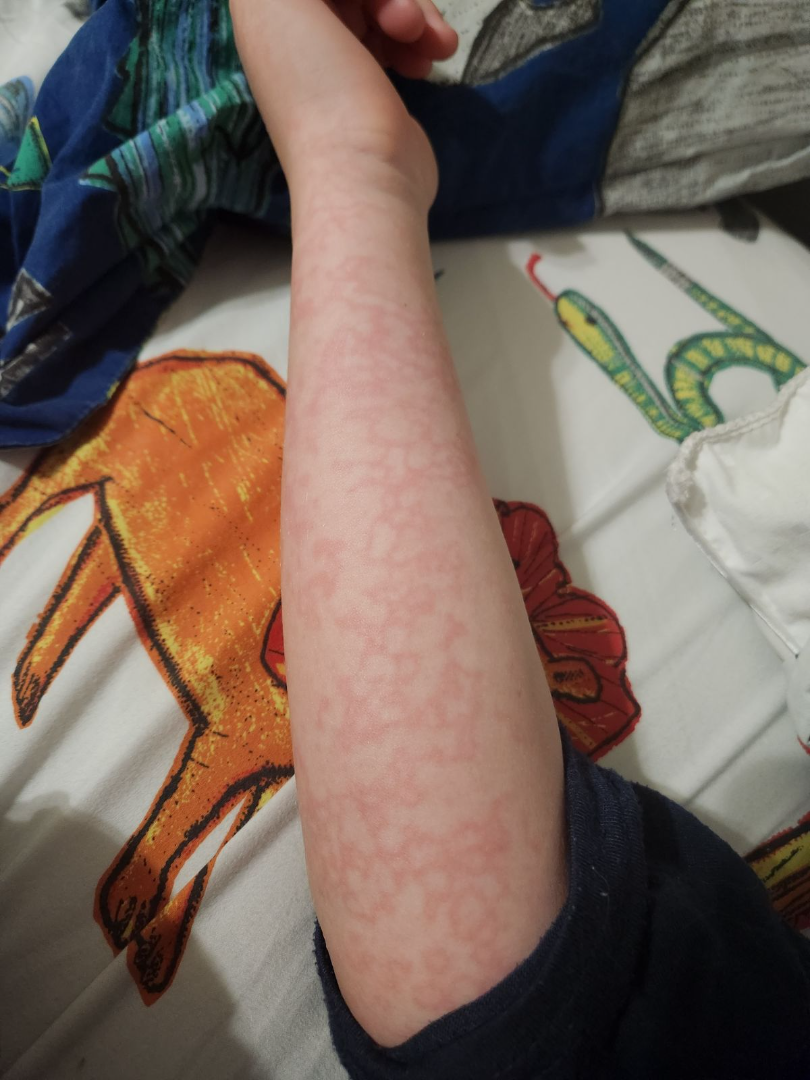The condition has been present for less than one week. Skin tone: FST II. This is a close-up image. The patient notes the lesion is flat. No constitutional symptoms were reported. The affected area is the front of the torso, arm and leg. Livedo reticularis (primary); Erythema ab igne (considered).